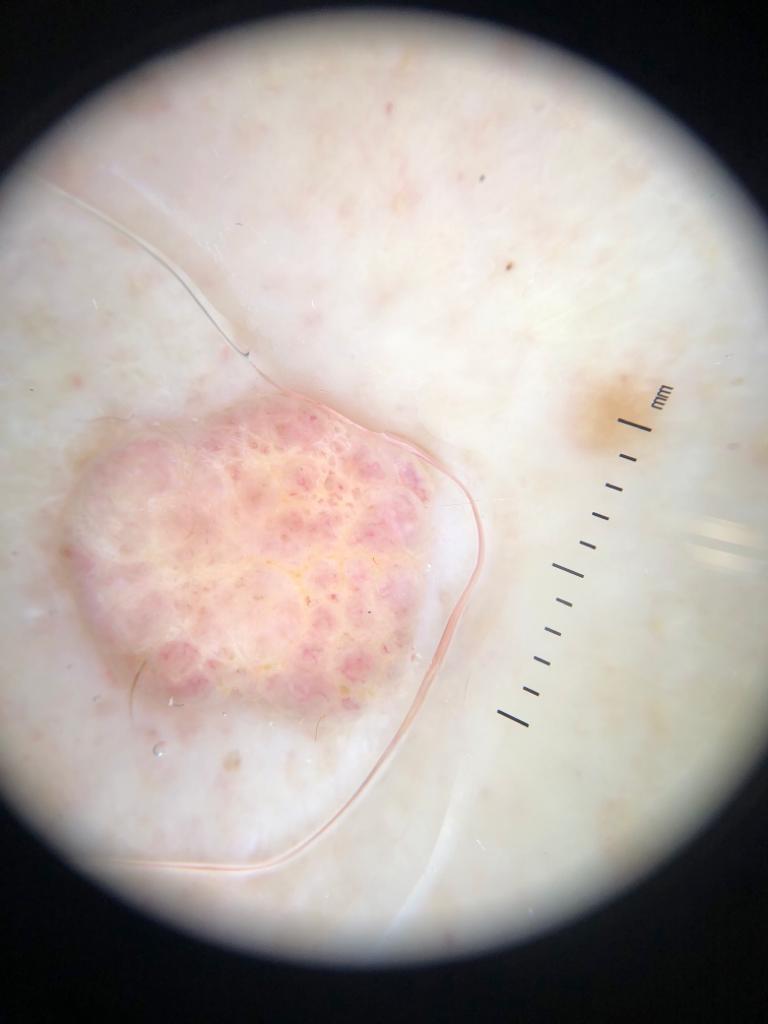patient = female, approximately 50 years of age
image type = contact-polarized dermoscopy
site = the trunk
diagnosis = Nevus (biopsy-proven)